The contributor is a female aged 18–29. The top or side of the foot, arm and back of the hand are involved. Close-up view.
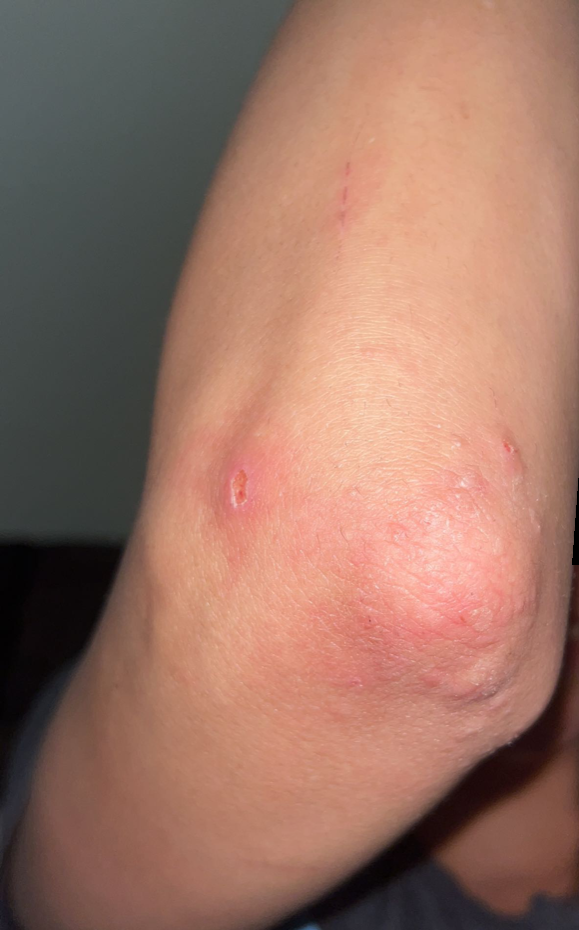Impression:
The favored diagnosis is Psoriasis; the differential also includes Dermatitis herpetiformis; a more distant consideration is Infected eczema; less probable is Foreign body reaction of the skin; less likely is Eczema.